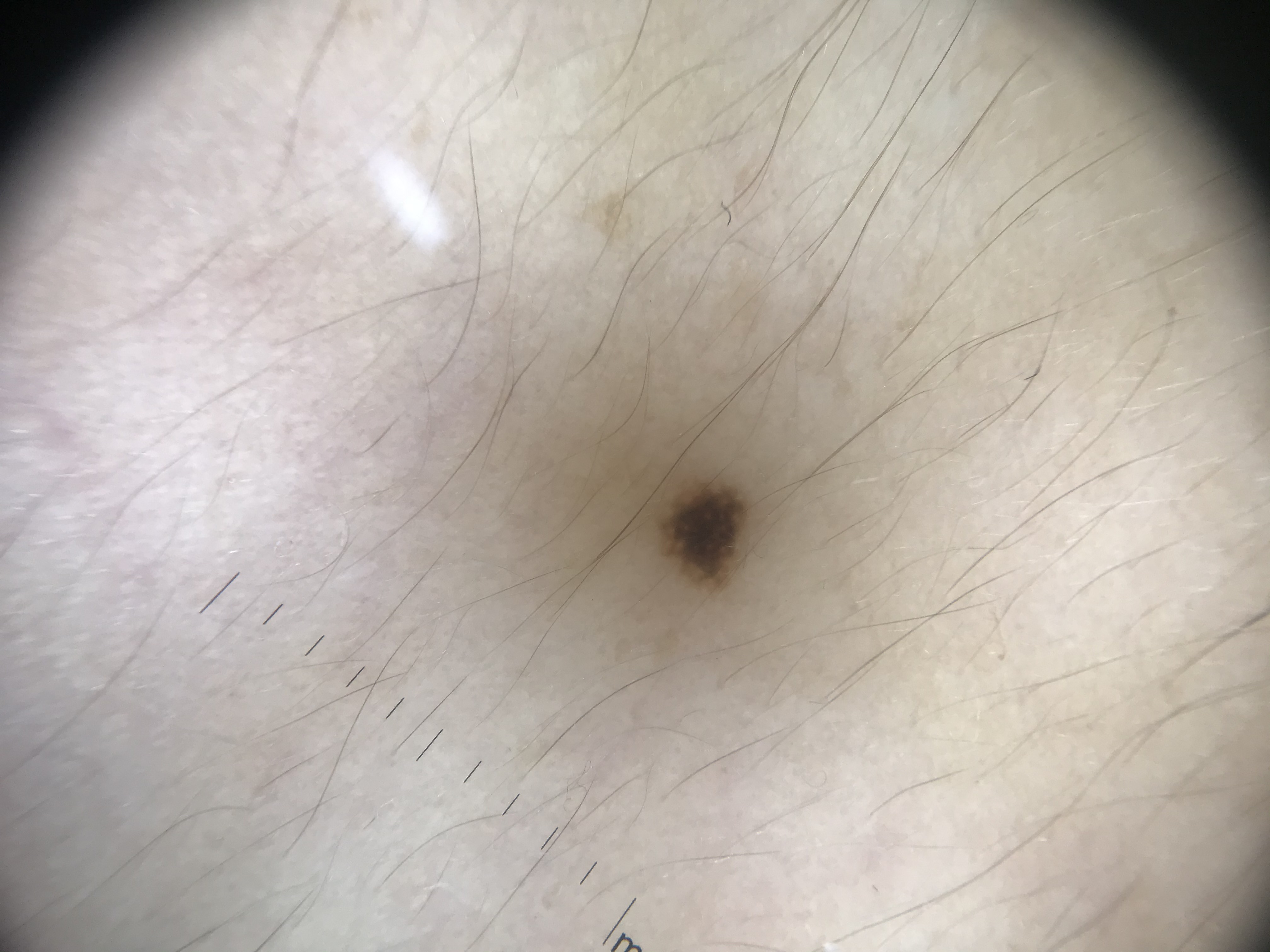A dermoscopic close-up of a skin lesion.
The morphology is that of a banal lesion.
The diagnosis was a junctional nevus.